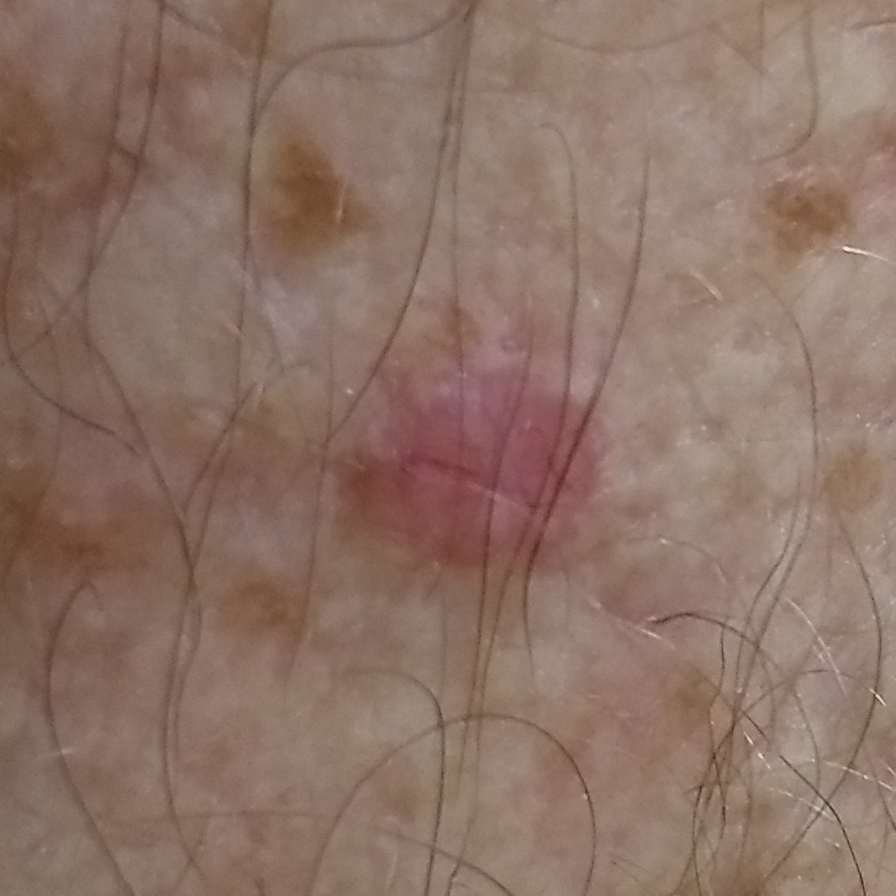The chart records prior skin cancer (patient or family) and alcohol use. The patient is FST I. A clinical photograph of a skin lesion. A male patient in their late 70s. Located on a forearm. Histopathologically confirmed as a skin cancer — a basal cell carcinoma.